This image was taken at a distance, the affected area is the head or neck, the contributor is a female aged 30–39: 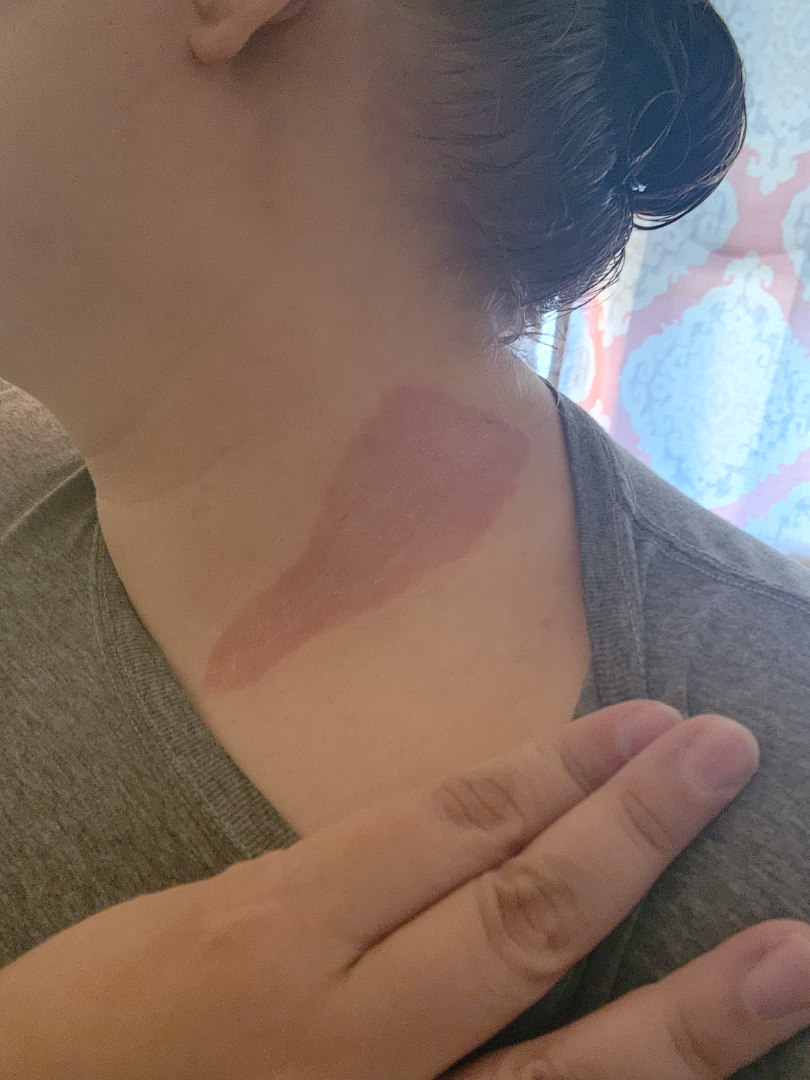The differential, in no particular order, includes Psoriasis, Burn erythema of neck and Allergic Contact Dermatitis.